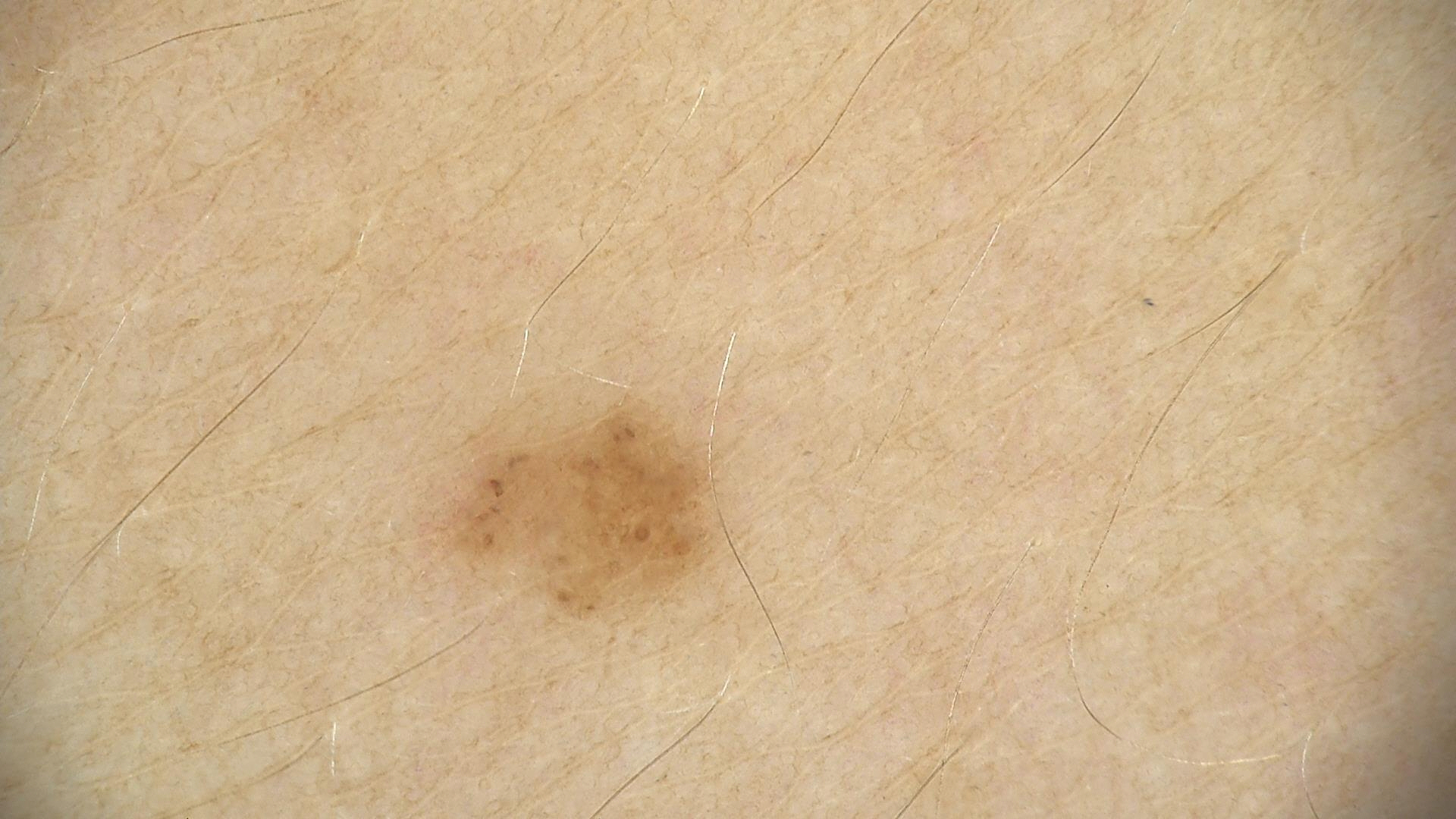{"diagnosis": {"name": "dysplastic junctional nevus", "code": "jd", "malignancy": "benign", "super_class": "melanocytic", "confirmation": "expert consensus"}}